This image was taken at a distance.
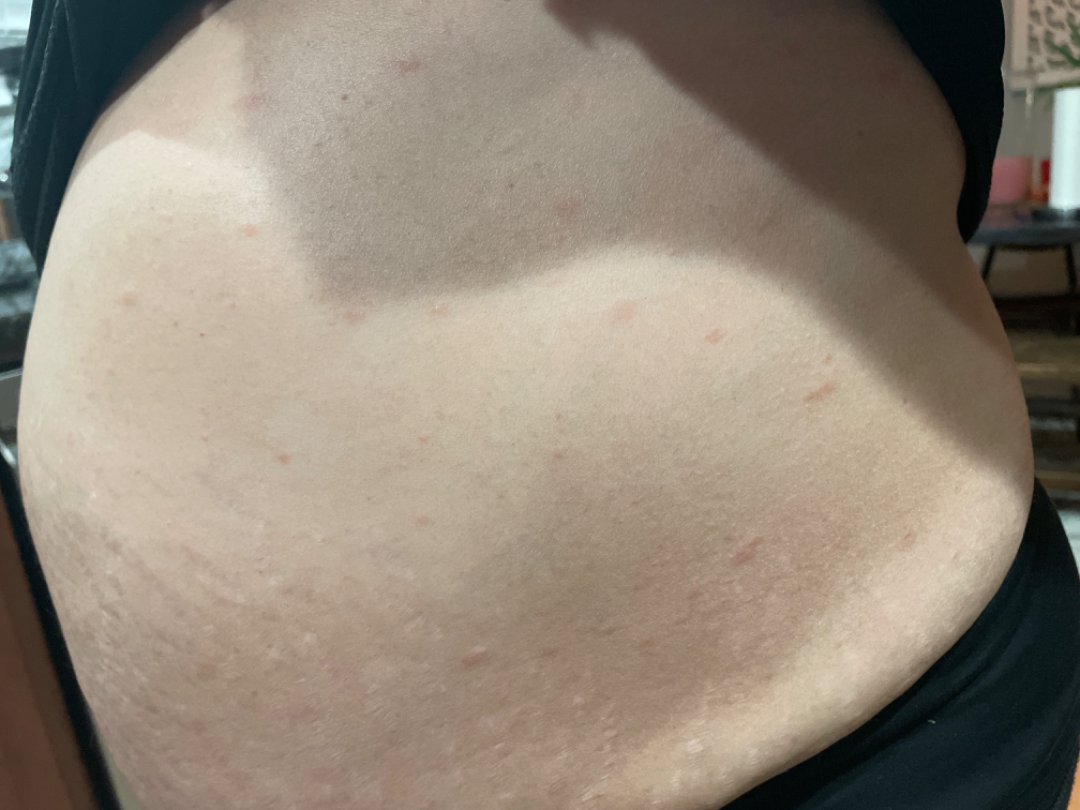The condition could not be reliably identified from the image.